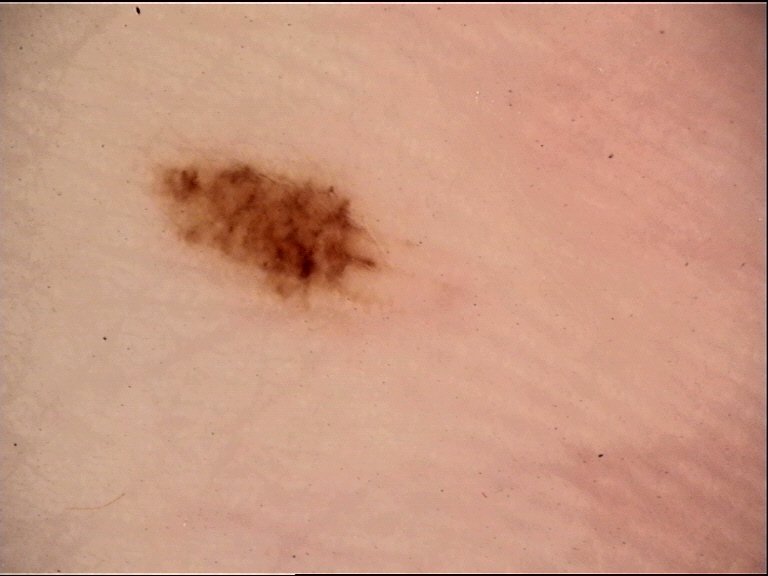A dermoscopic image of a skin lesion.
The diagnosis was an acral dysplastic junctional nevus.